A dermoscopic close-up of a skin lesion · a male subject, aged 33 to 37: 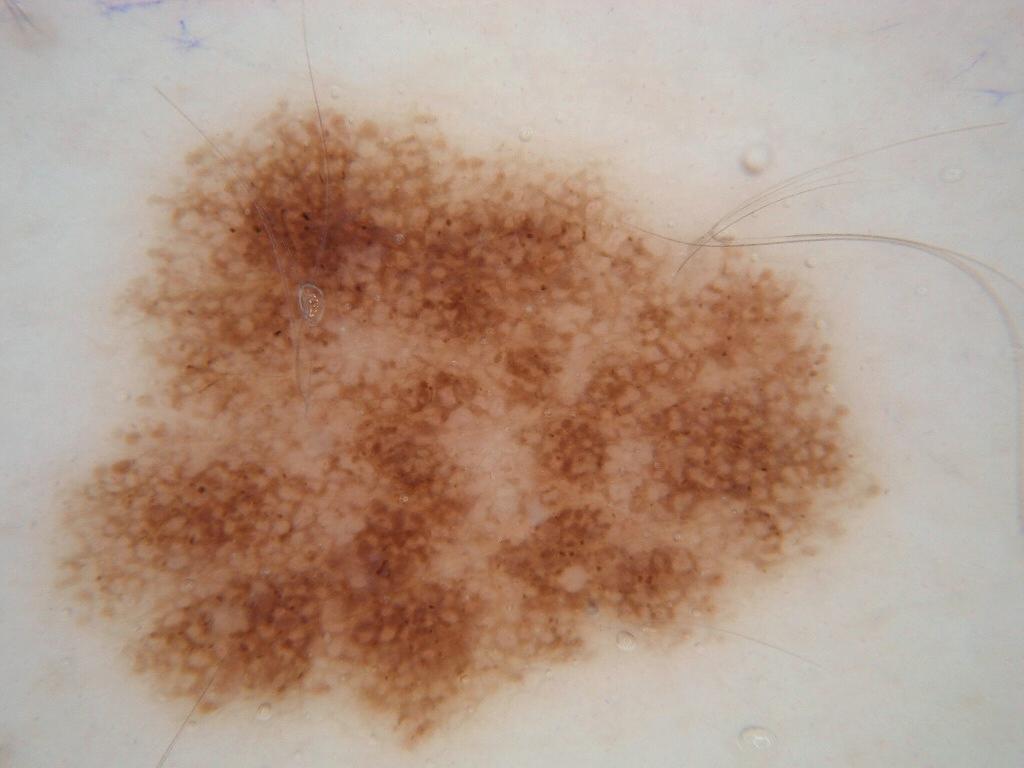Case summary:
* lesion location — x1=53, y1=89, x2=894, y2=757
* dermoscopic features — pigment network, milia-like cysts, globules, and streaks; absent: negative network
* extent — ~51% of the field
* impression — a melanocytic nevus, a benign skin lesion